The lesion is described as raised or bumpy and fluid-filled. The leg is involved. The patient considered this a rash. Fitzpatrick II; human graders estimated a MST of 2. The patient indicates the condition has been present for about one day. The lesion is associated with itching and bothersome appearance. The photo was captured at an angle. The contributor is 60–69, female:
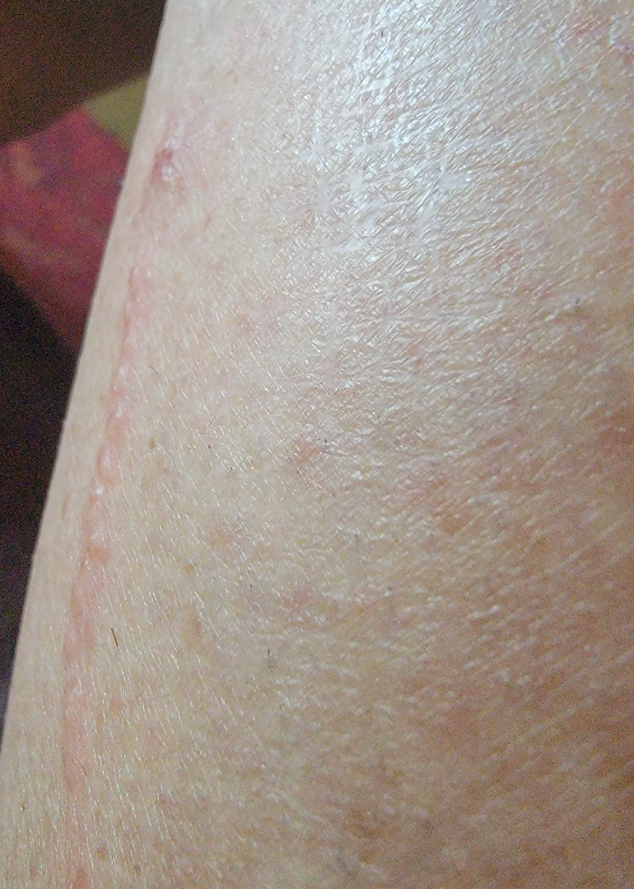On dermatologist assessment of the image, most consistent with Lichen striatus; possibly Herpes Zoster; the differential also includes Allergic Contact Dermatitis.